A male subject in their 80s. A dermatoscopic image of a skin lesion.
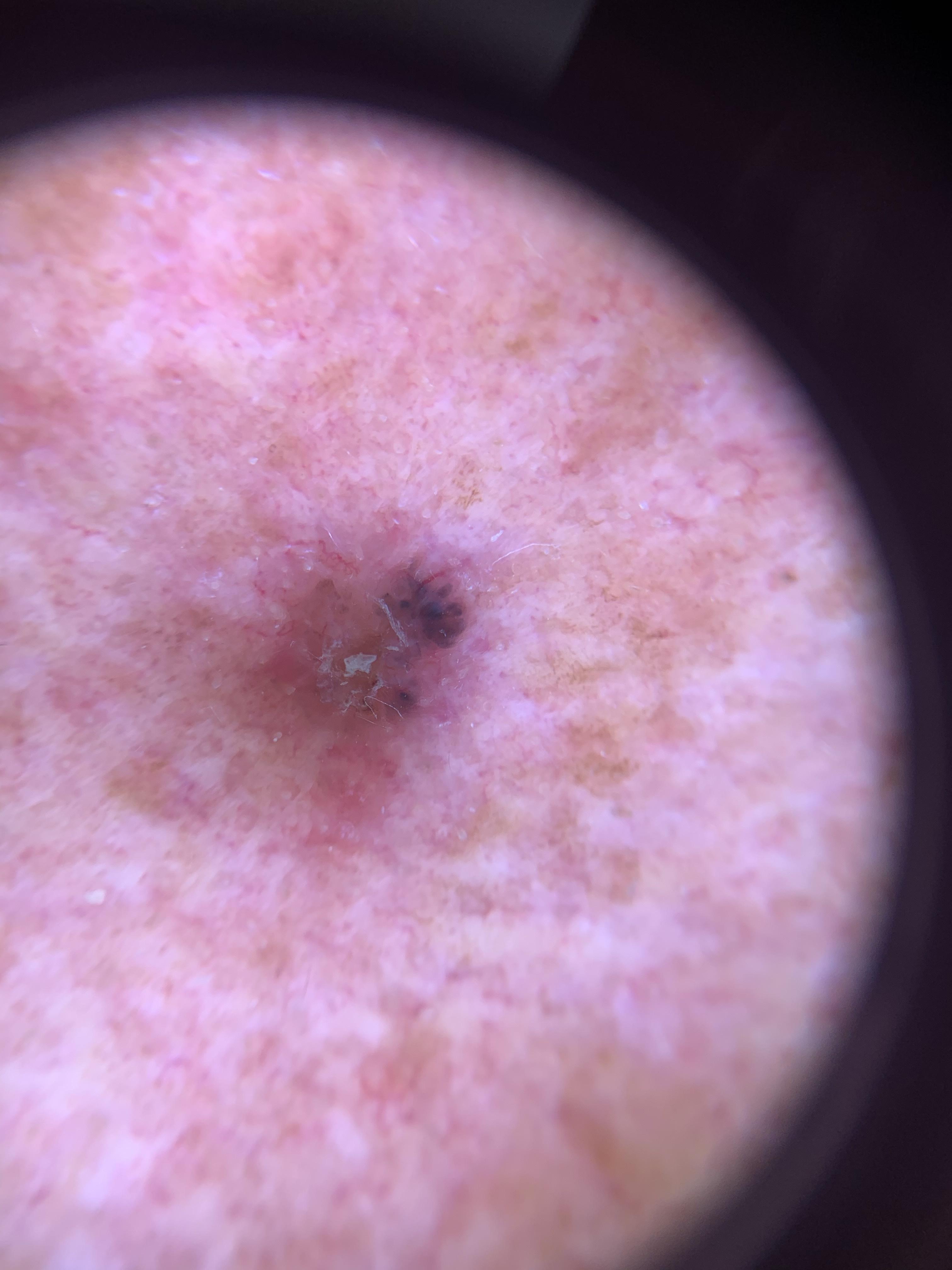The lesion is on the head or neck.
Histopathologically confirmed as a benign, epidermal lesion — a seborrheic keratosis.